Dermoscopy of a skin lesion.
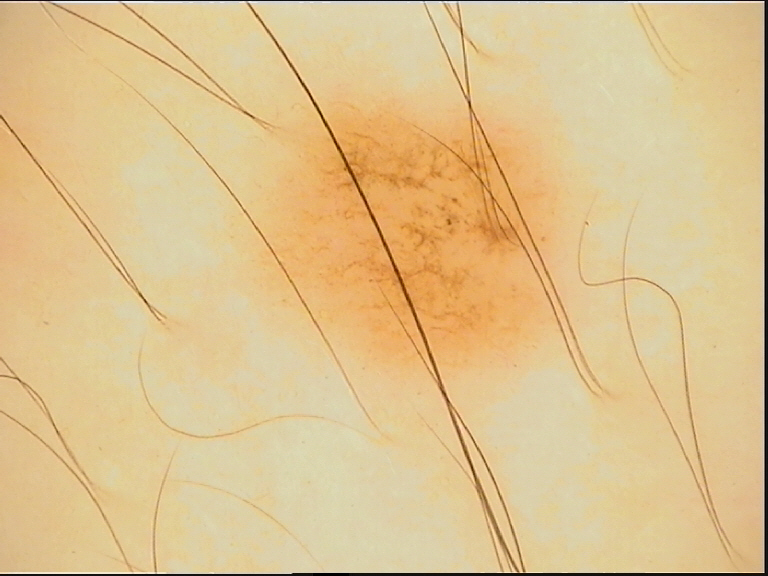The diagnostic label was a benign lesion — a dysplastic junctional nevus.